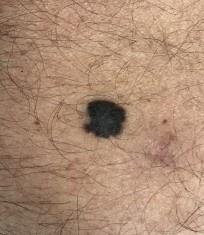Findings:
- imaging · clinical photo (overview)
- subject · male, aged around 70
- Fitzpatrick · II
- diagnosis · Melanoma (biopsy-proven)